Texture is reported as rough or flaky, fluid-filled and raised or bumpy · the contributor notes the condition has been present for one to four weeks · the patient described the issue as a rash · the arm is involved · female patient, age 50–59 · the photograph was taken at a distance.
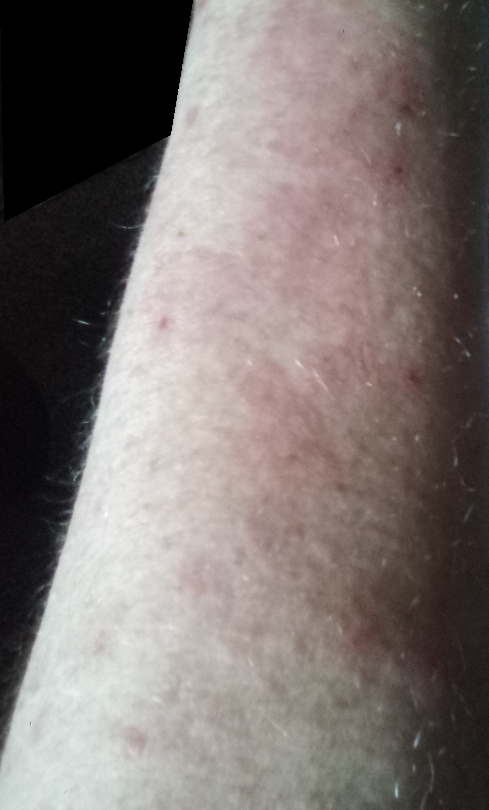{"assessment": "could not be assessed"}